A clinical close-up photograph of a skin lesion.
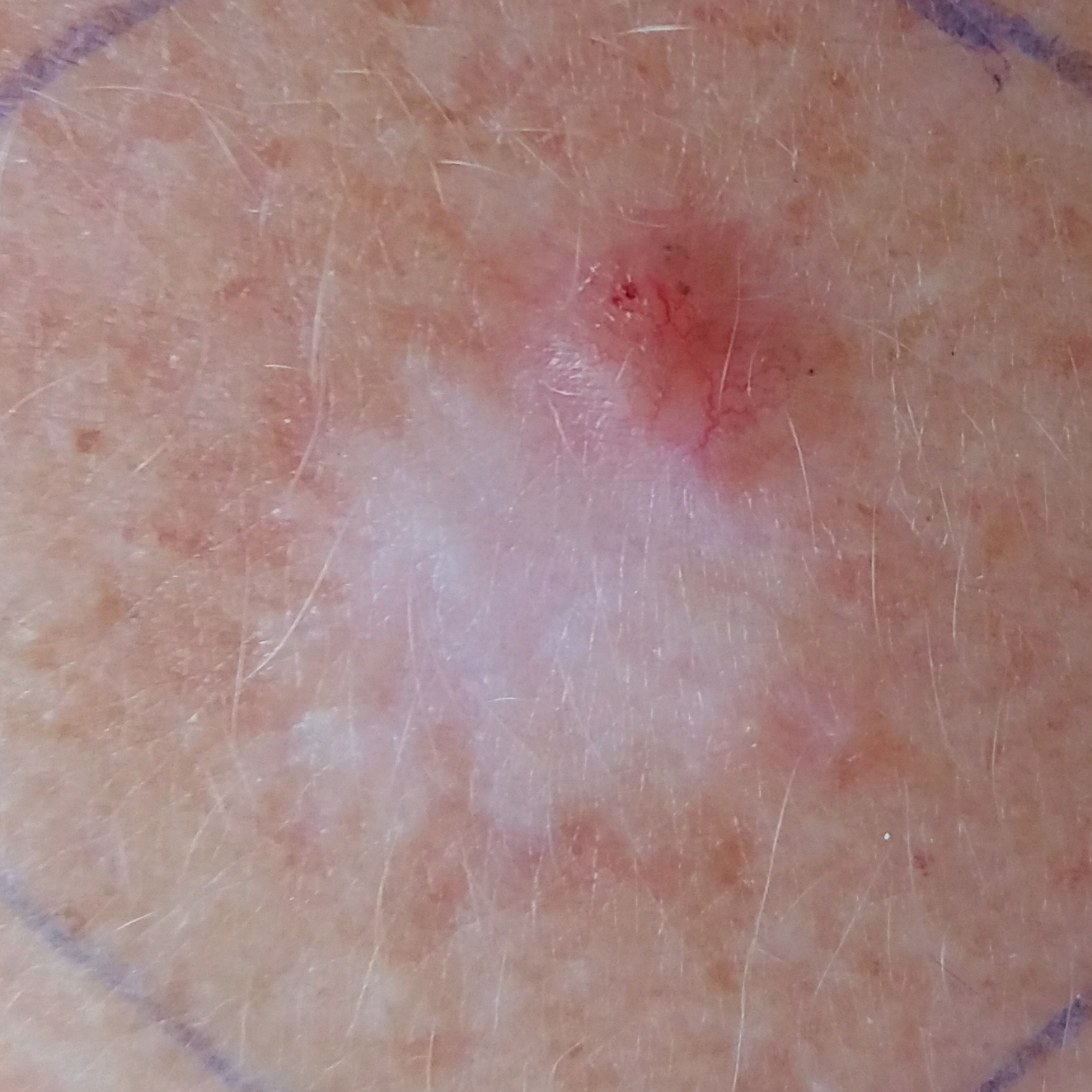| key | value |
|---|---|
| symptoms | change in appearance, elevation, itching, growth, bleeding / no pain |
| diagnosis | basal cell carcinoma (biopsy-proven) |